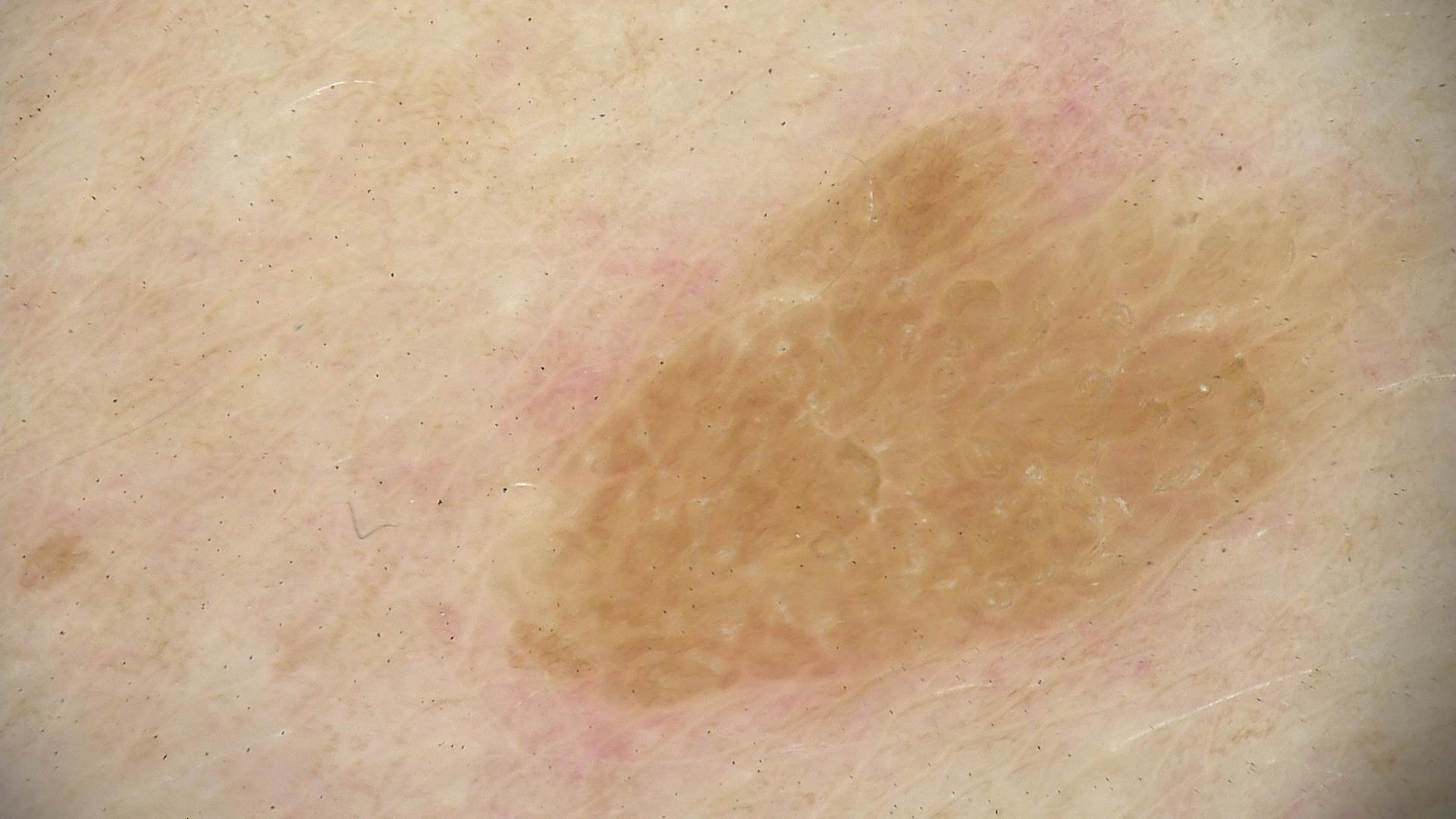Case:
* image type — dermatoscopy
* label — seborrheic keratosis (expert consensus)